The lesion is associated with itching; reported duration is less than one week; this image was taken at a distance; the lesion is described as raised or bumpy; the patient considered this a rash: 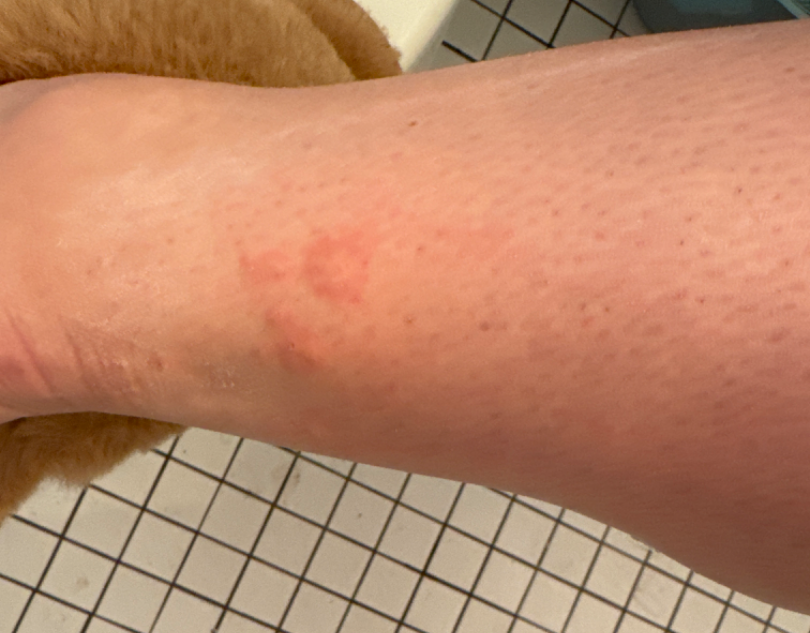Q: What is the differential diagnosis?
A: a single dermatologist reviewed the case: most consistent with Insect Bite; also on the differential is Urticaria; also raised was Animal bite - wound